A dermatoscopic image of a skin lesion.
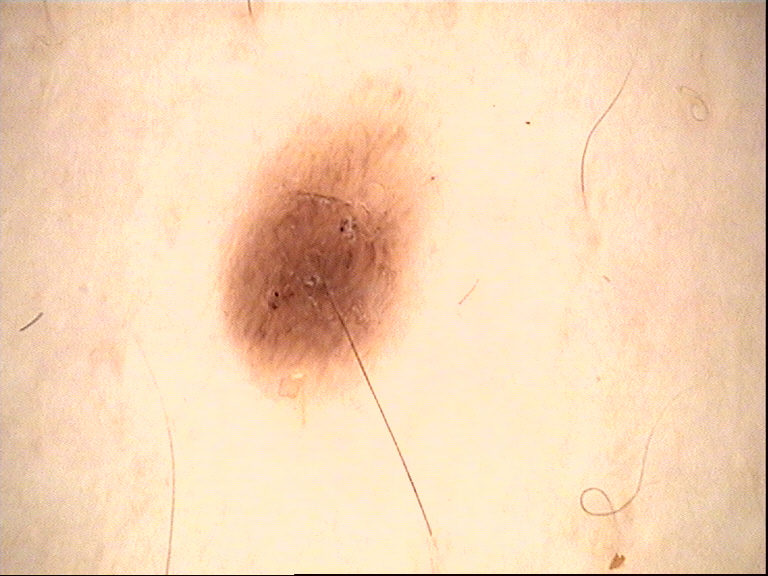The morphology is that of a banal lesion. Consistent with a junctional nevus.